This is a close-up image. Located on the arm and leg. Female patient, age 30–39:
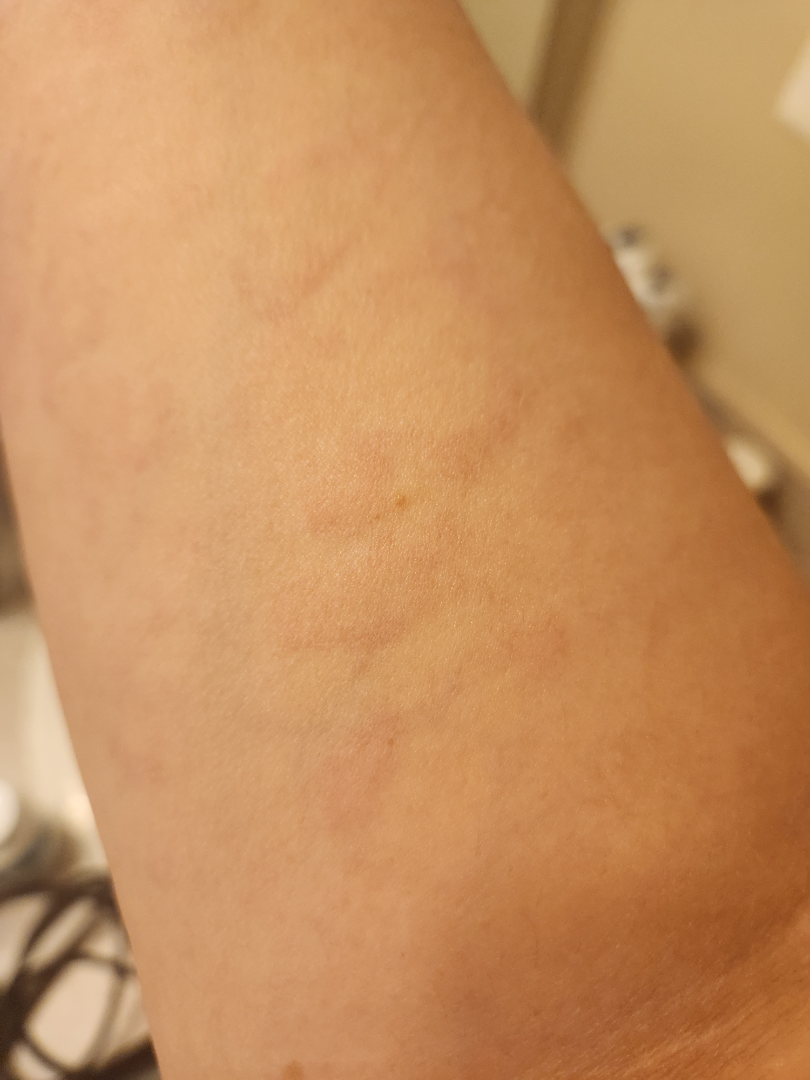The case was difficult to assess from the available photograph. No constitutional symptoms were reported. Fitzpatrick IV; lay graders estimated Monk skin tone scale 2 or 4 (two reviewer pools disagreed). Reported duration is about one day. The lesion is associated with enlargement and itching. The patient described the issue as a rash.